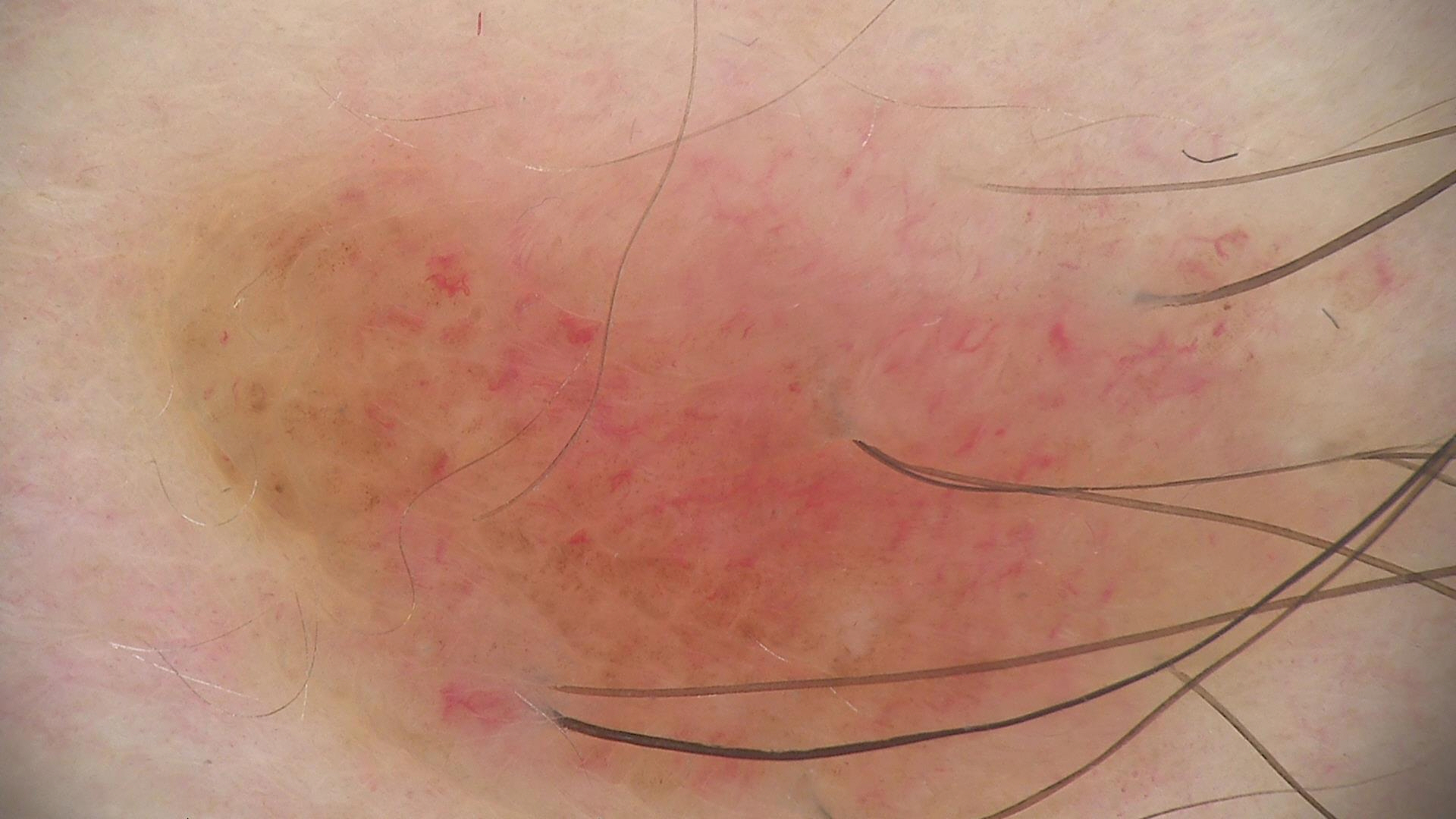Findings:
- label — compound nevus (expert consensus)